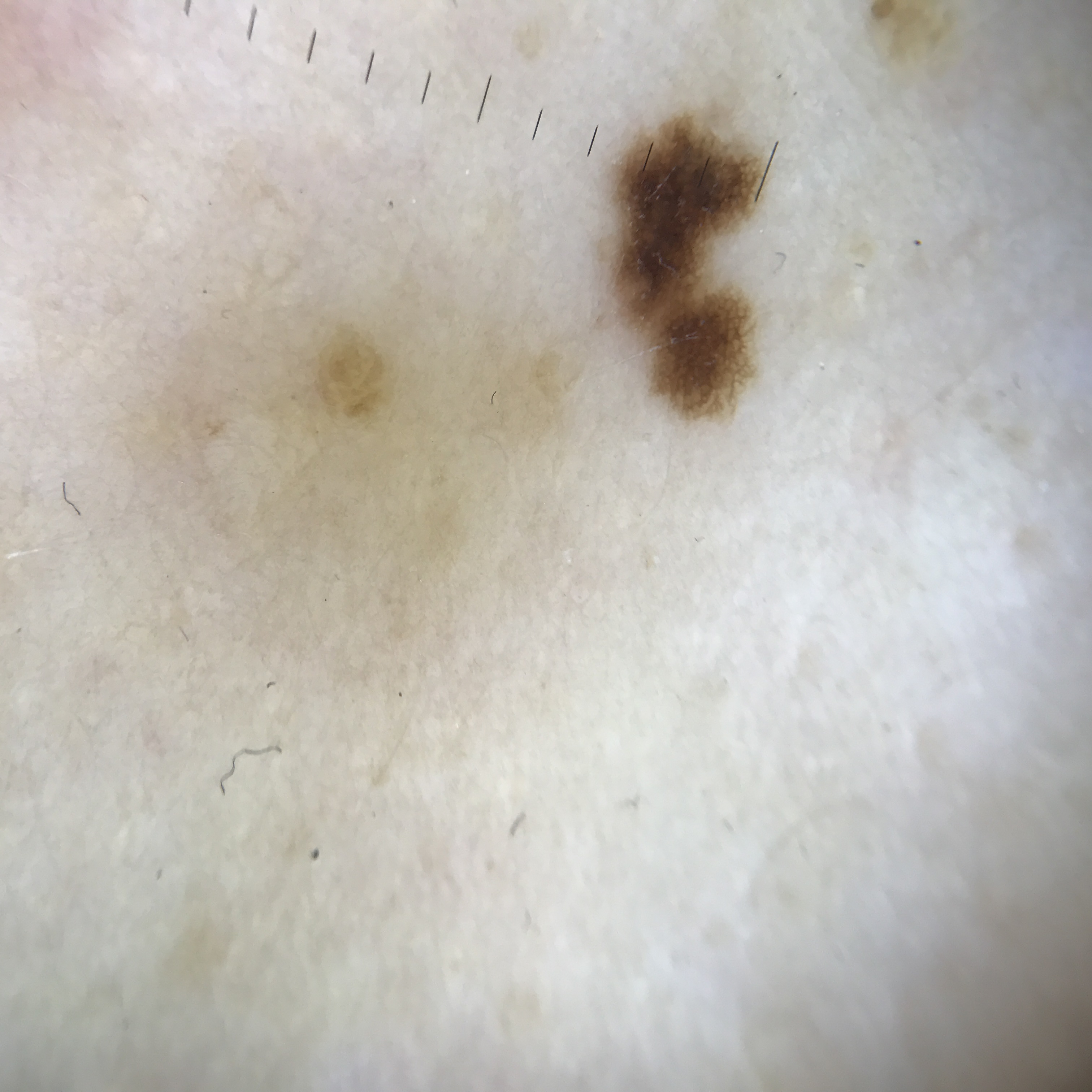modality: dermoscopy
diagnostic label: dysplastic junctional nevus (expert consensus)